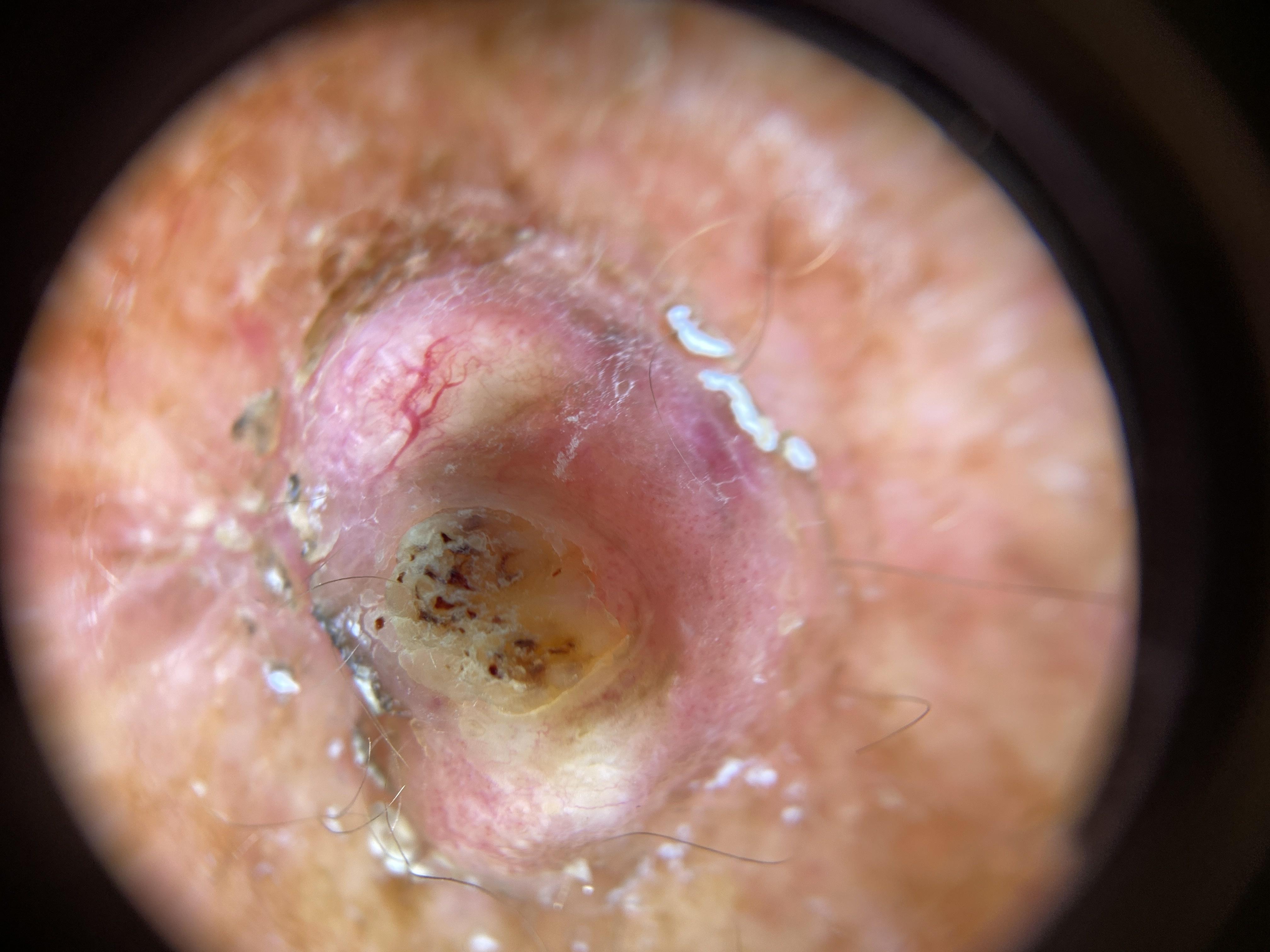Dermoscopy of a skin lesion. Fitzpatrick phototype II. Located on an upper extremity. On biopsy, the diagnosis was a malignancy — a squamous cell carcinoma.